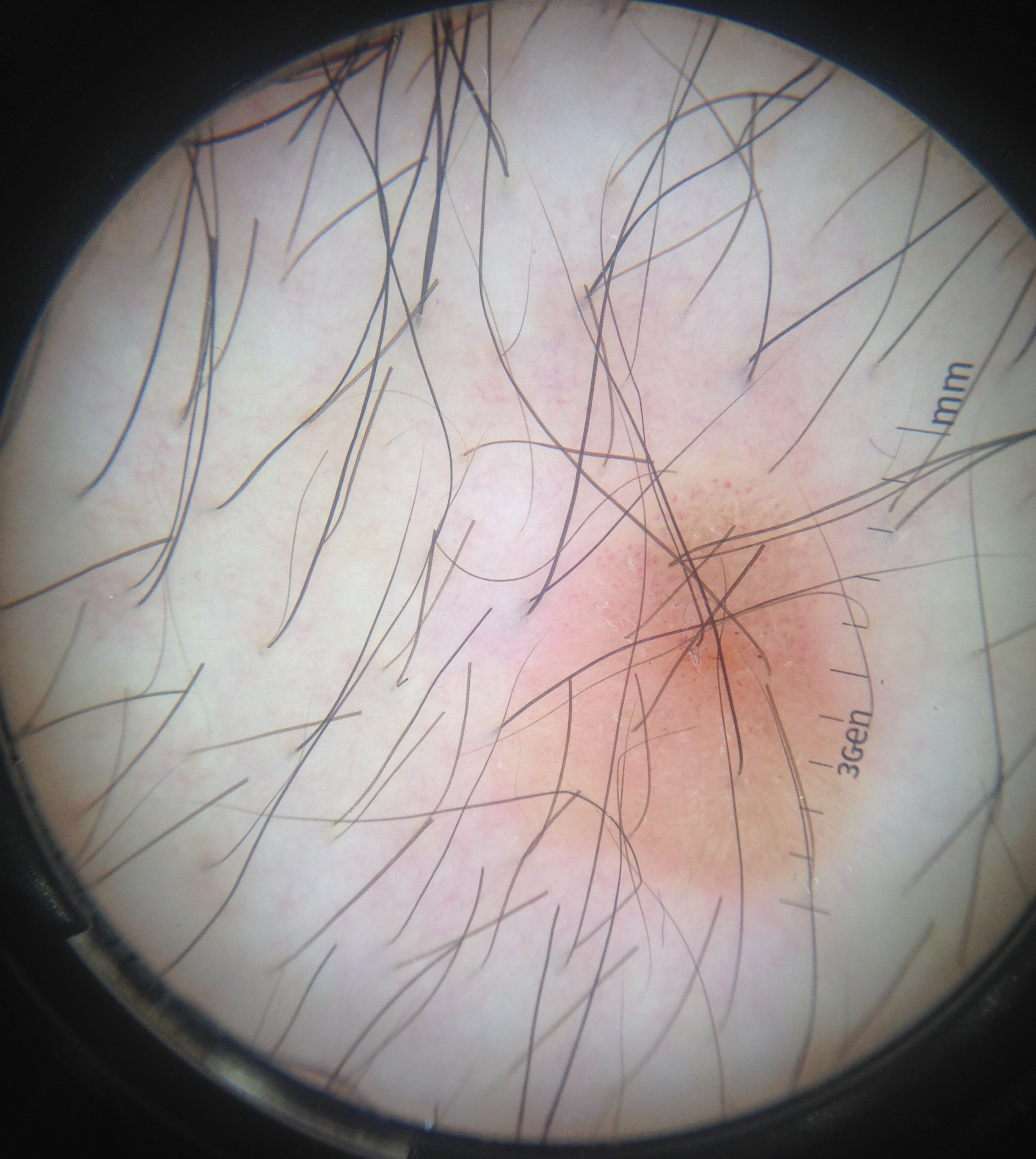Labeled as a seborrheic keratosis.